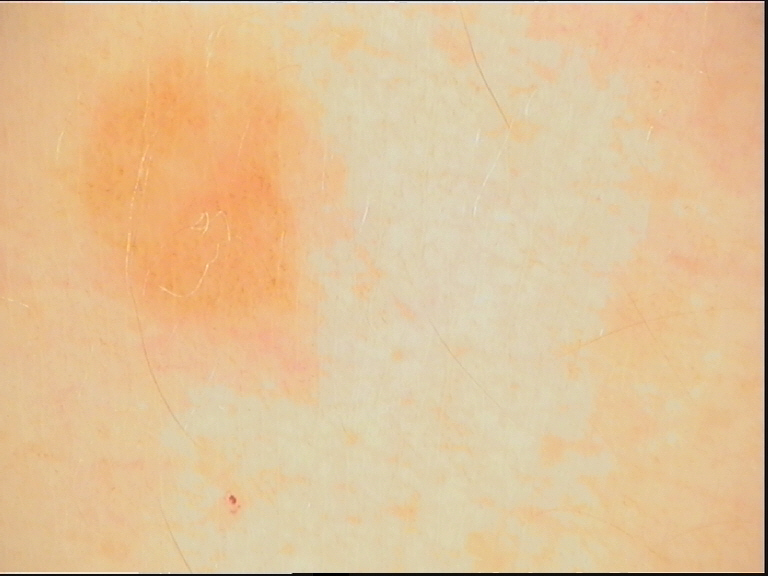Dermoscopy of a skin lesion.
The morphology is that of a banal lesion.
Labeled as a junctional nevus.